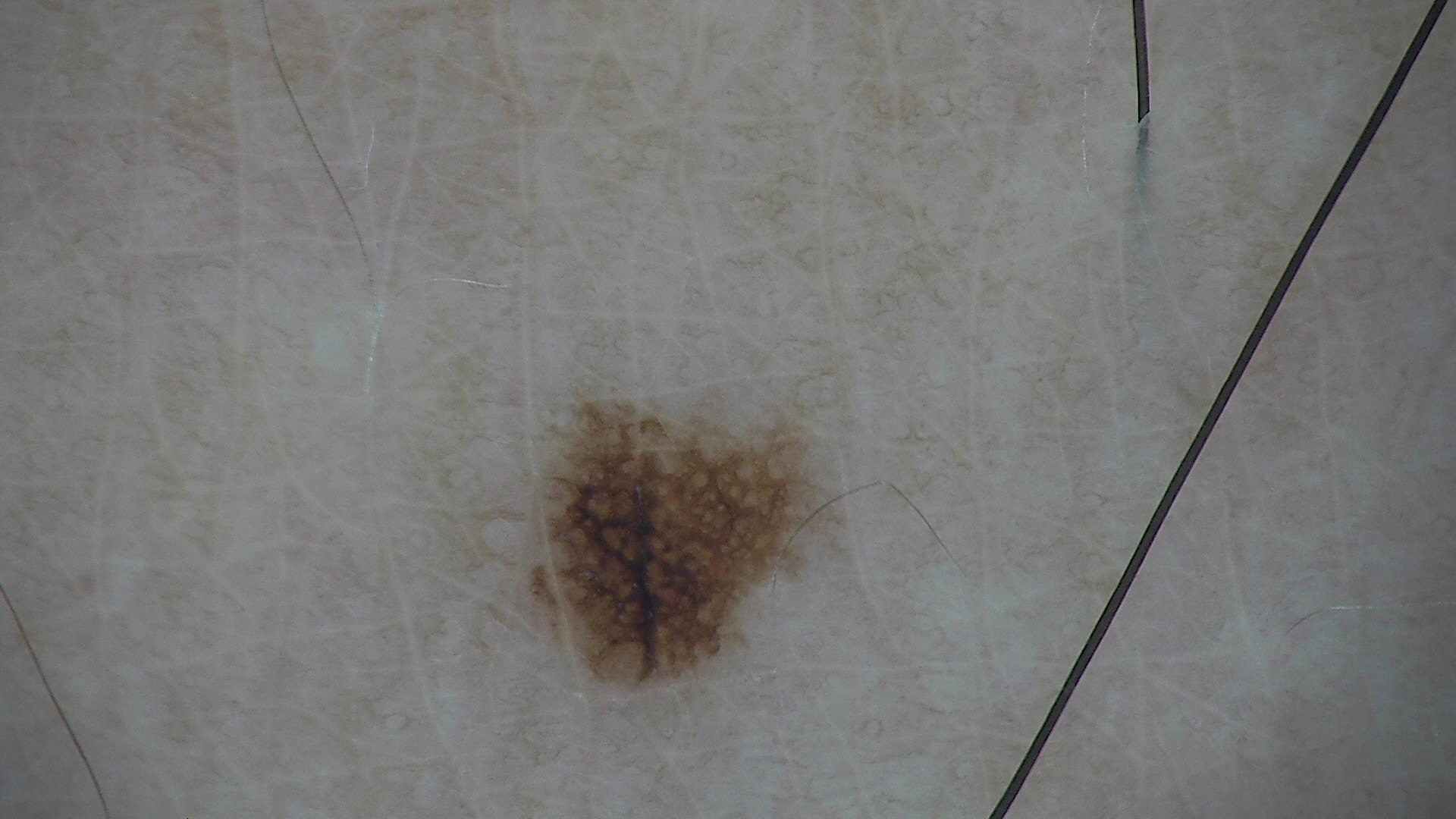Impression: Classified as a benign lesion — a dysplastic junctional nevus.